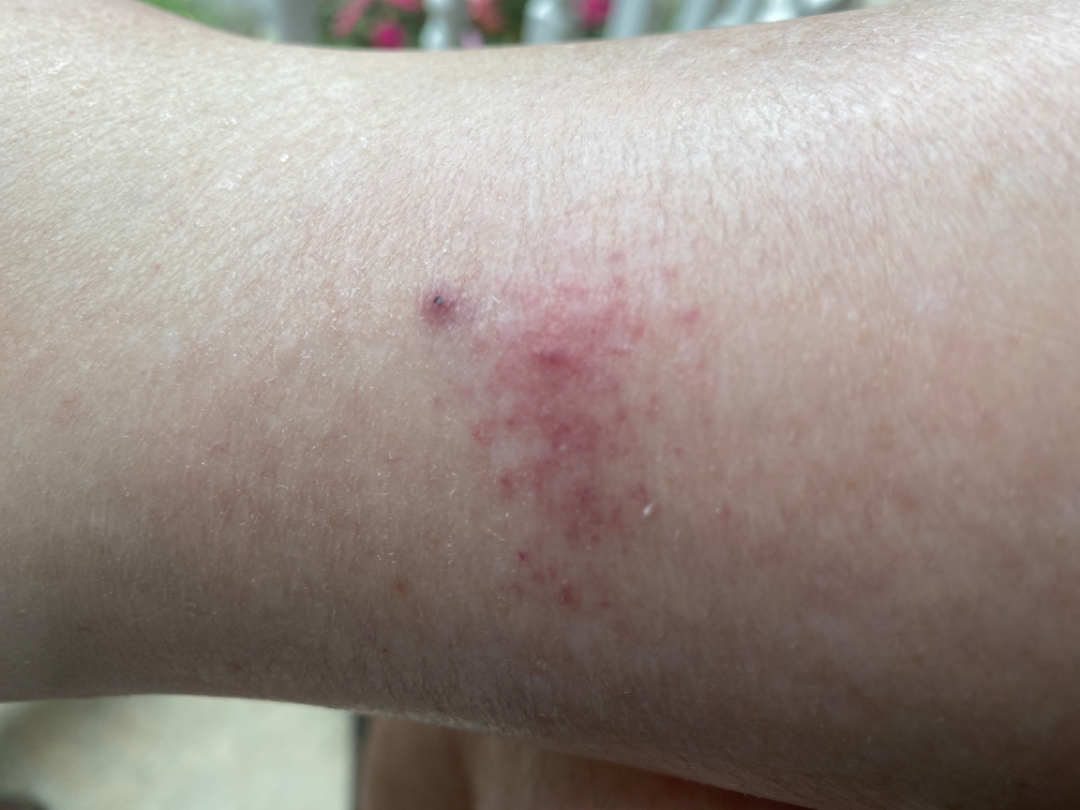| key | value |
|---|---|
| onset | less than one week |
| lesion symptoms | pain |
| constitutional symptoms | none reported |
| self-categorized as | a rash |
| lesion texture | raised or bumpy |
| location | leg |
| image framing | close-up |
| dermatologist impression | Allergic Contact Dermatitis (54%); Insect Bite (23%); Eczema (23%) |